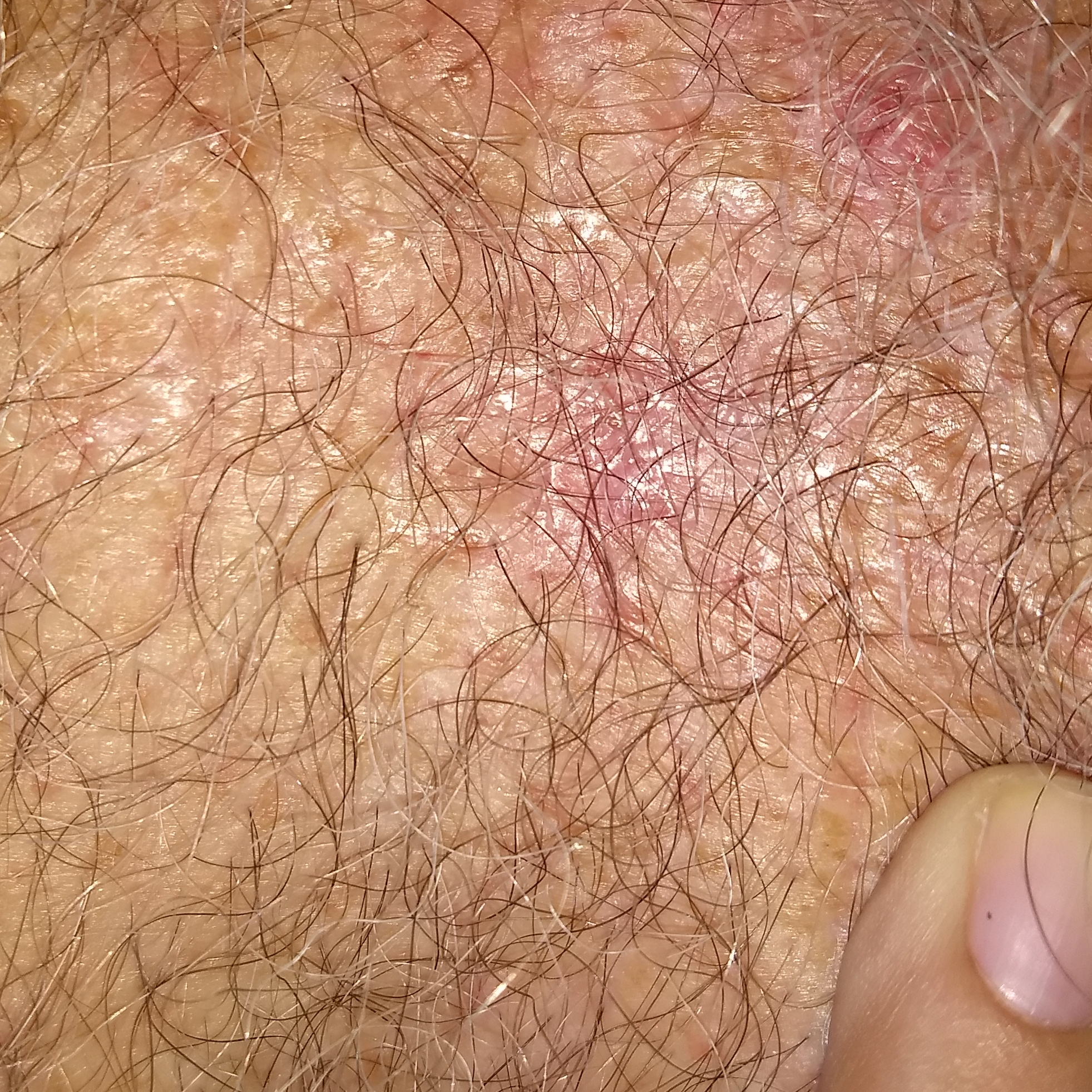Q: What is the patient's skin type?
A: II
Q: How was this image acquired?
A: clinical photo
Q: Patient demographics?
A: male, in their 60s
Q: What are the relevant risk factors?
A: pesticide exposure, prior skin cancer (patient or family), alcohol use
Q: Where on the body is the lesion?
A: the back
Q: What are the lesion's dimensions?
A: 15x12 mm
Q: What does the patient describe?
A: itching, bleeding
Q: What was the clinical impression?
A: actinic keratosis (clinical consensus)